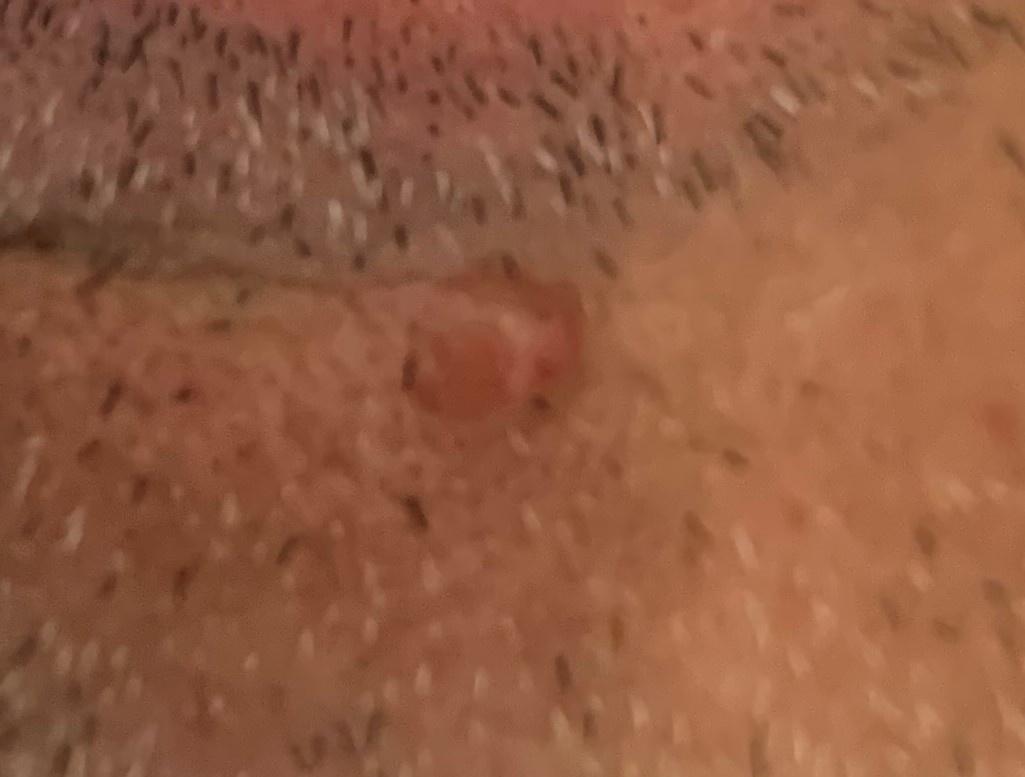Findings: A male patient about 65 years old. The lesion is located on the head or neck. Diagnosis: Confirmed on histopathology as a malignant, adnexal lesion — a basal cell carcinoma.